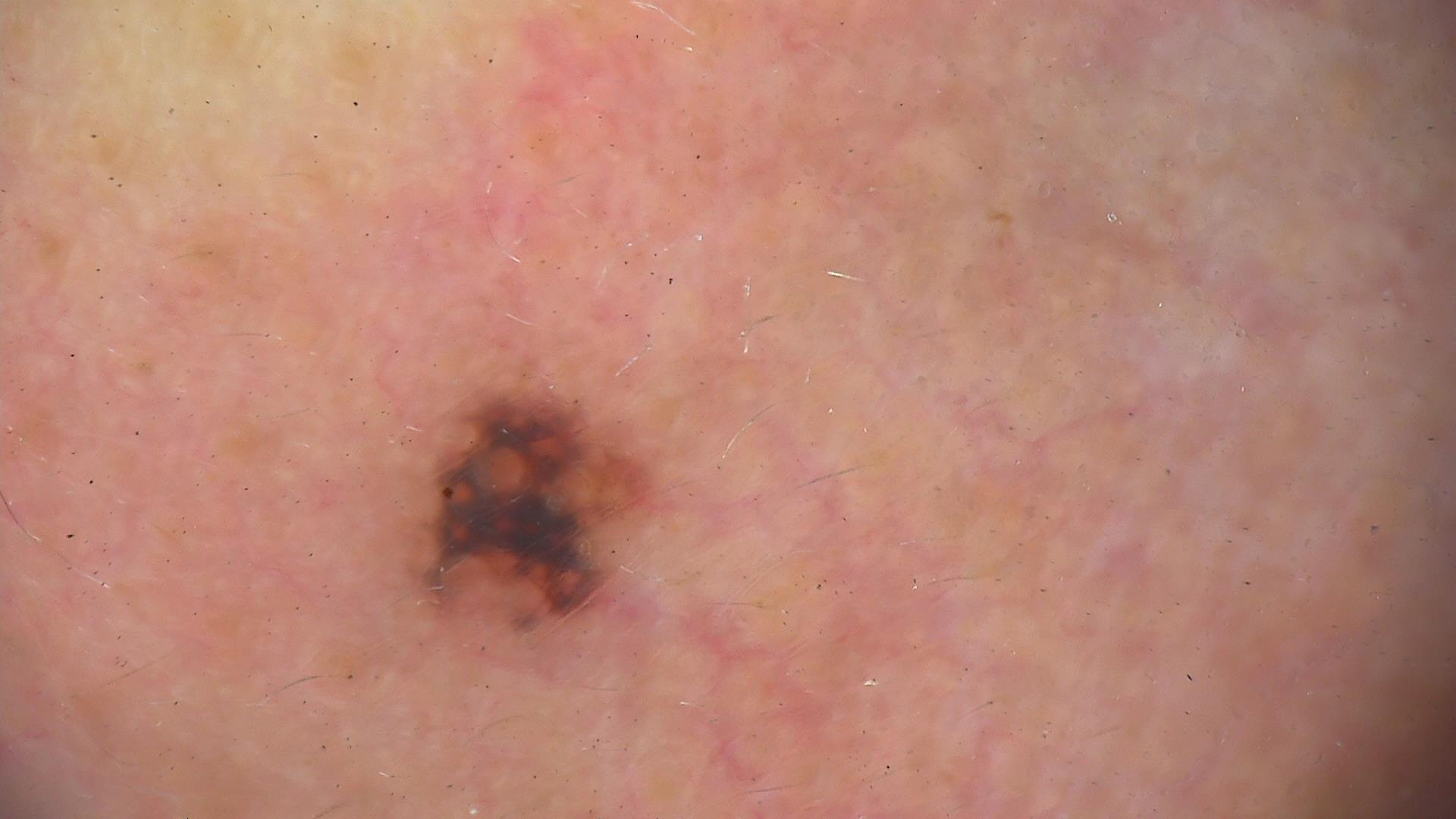Findings:
• class · dysplastic junctional nevus (expert consensus)